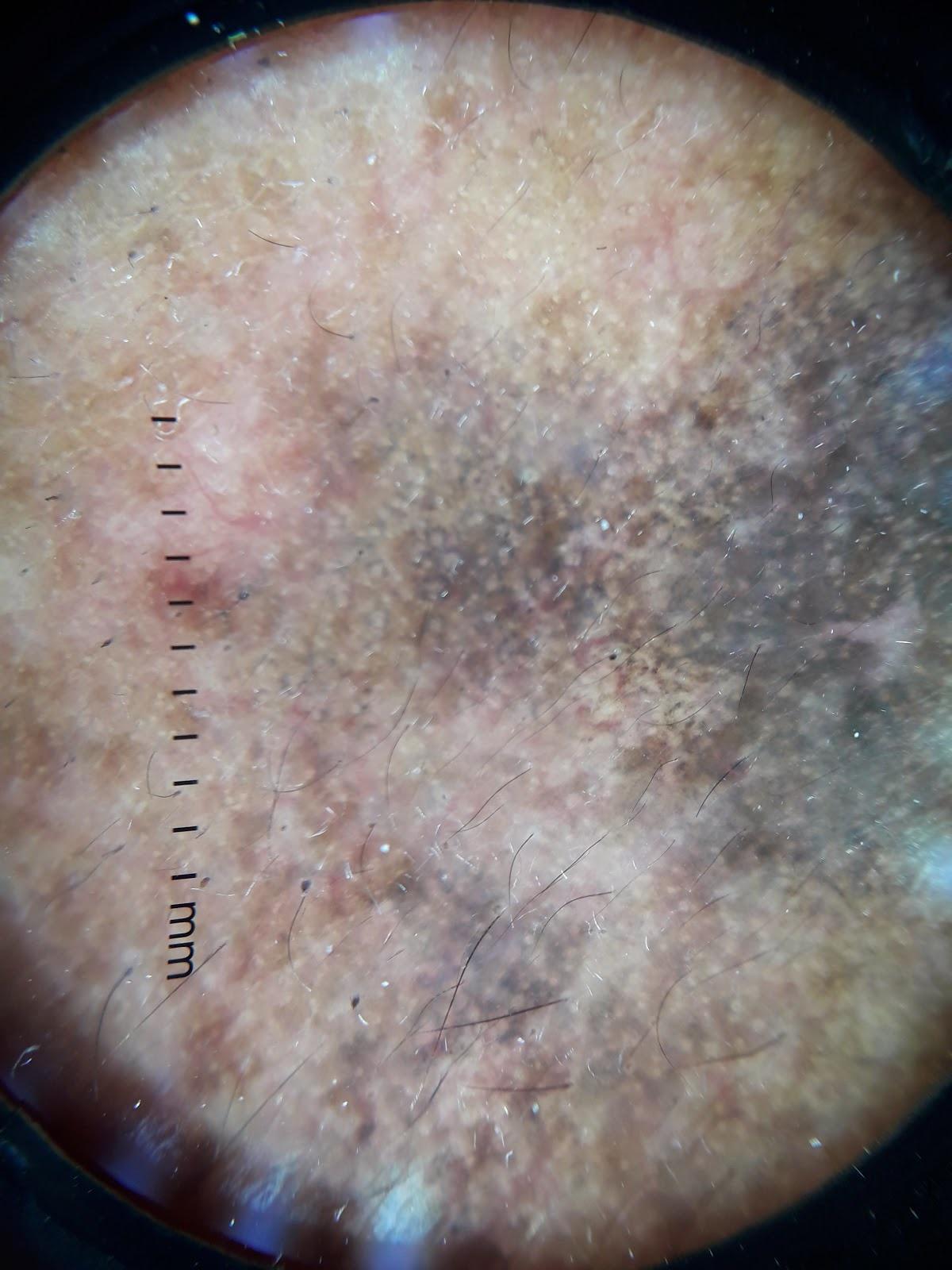Q: What is the melanoma history?
A: a prior melanoma
Q: How was this image acquired?
A: dermatoscopic image
Q: What are the patient's age and sex?
A: male, in their mid- to late 60s
Q: Where on the body is the lesion?
A: the head or neck
Q: What is the diagnosis?
A: Melanoma (biopsy-proven)